A skin lesion imaged with a dermatoscope.
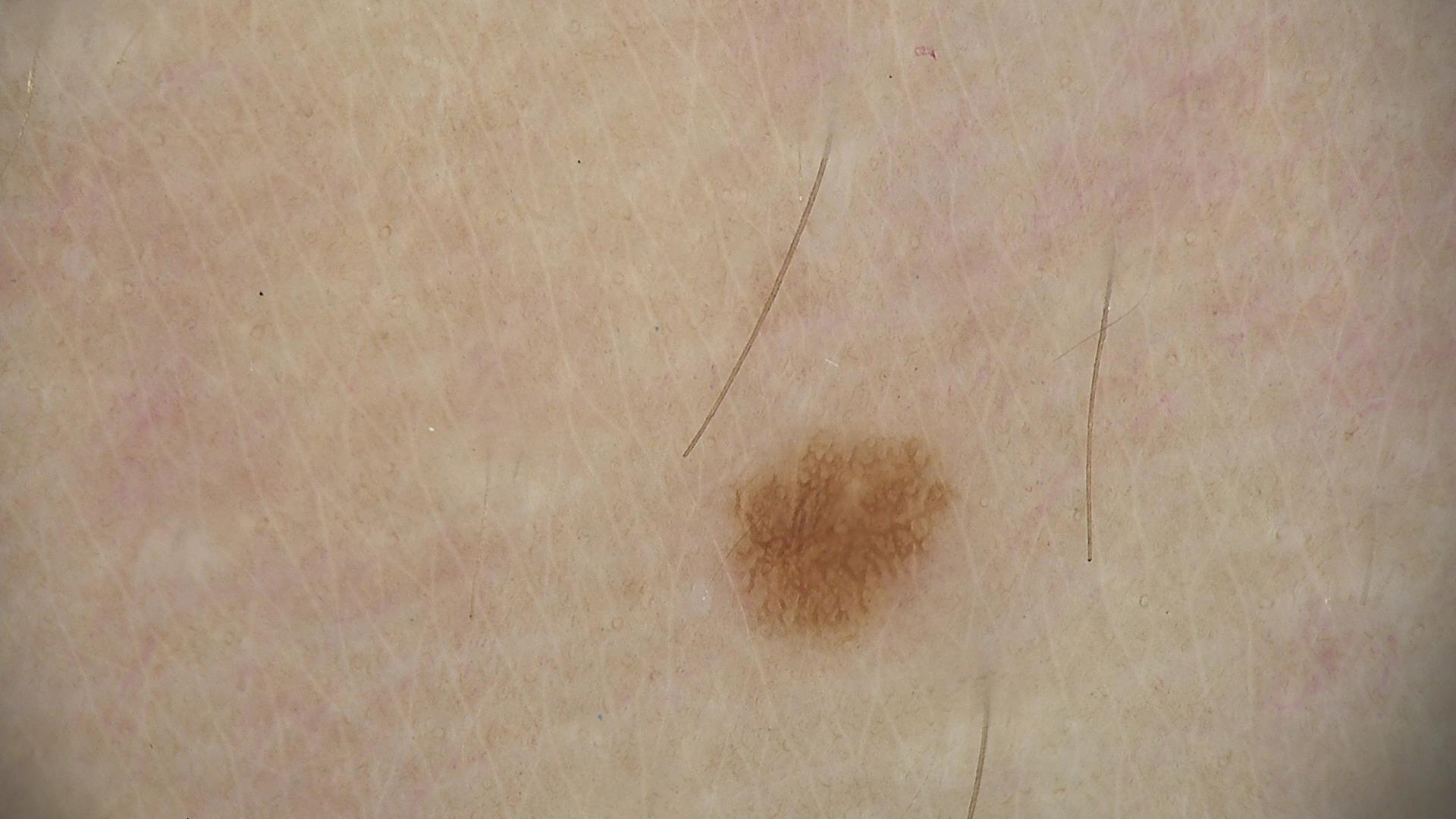<case>
  <diagnosis>
    <name>junctional nevus</name>
    <code>jb</code>
    <malignancy>benign</malignancy>
    <super_class>melanocytic</super_class>
    <confirmation>expert consensus</confirmation>
  </diagnosis>
</case>